A dermoscopic close-up of a skin lesion: 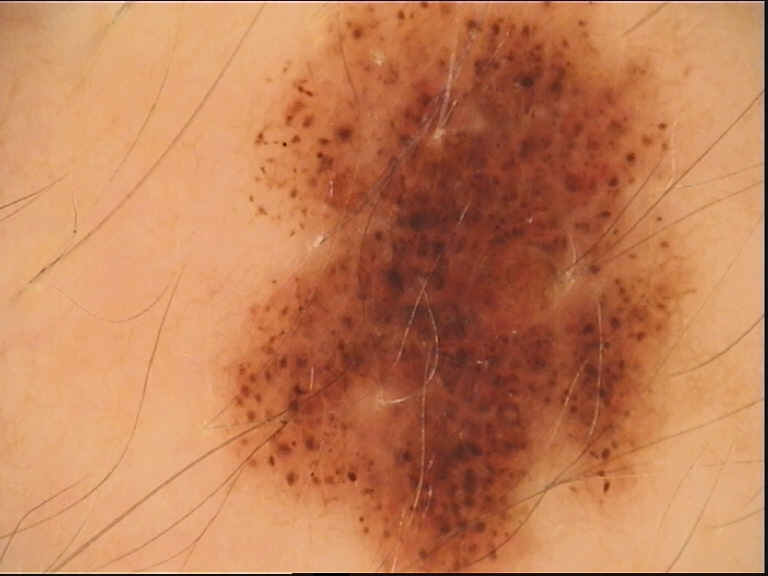Case:
* class · dysplastic junctional nevus (expert consensus)